A male patient aged around 50 · Fitzpatrick phototype II · an overview clinical photograph of a skin lesion · the chart records a previous melanoma but no first-degree relative with melanoma:
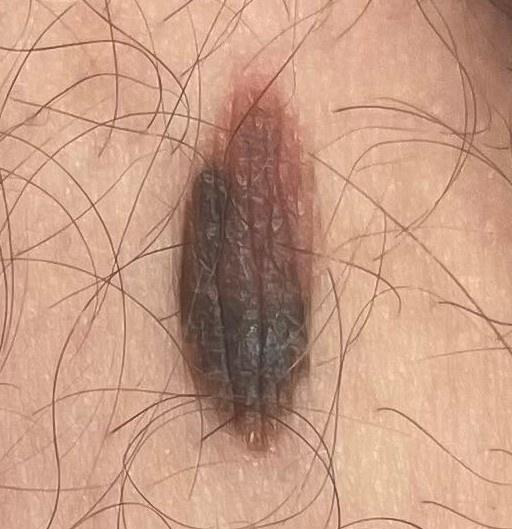body site: a lower extremity | diagnostic label: Melanoma (biopsy-proven).